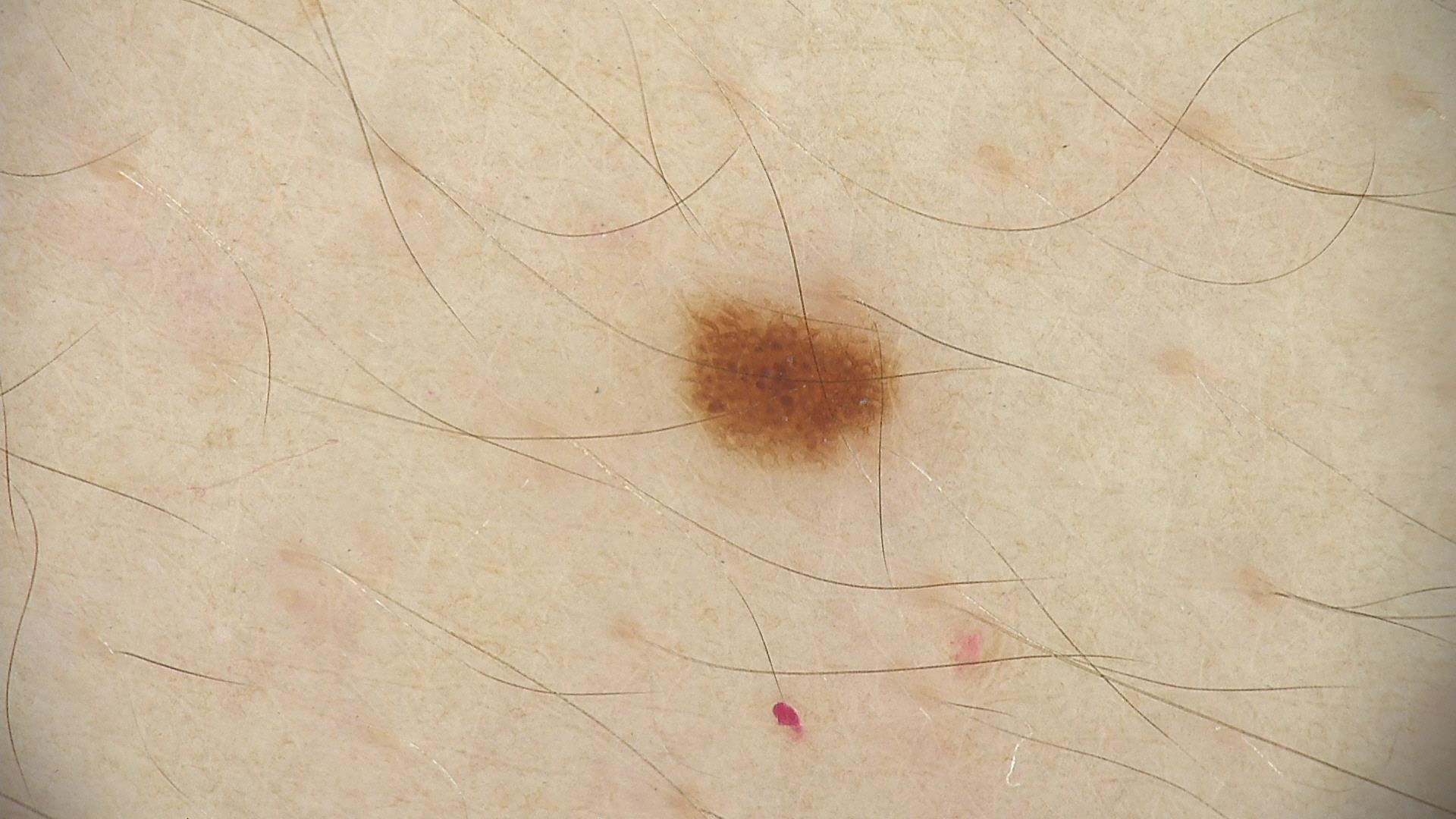diagnosis: dysplastic junctional nevus (expert consensus).